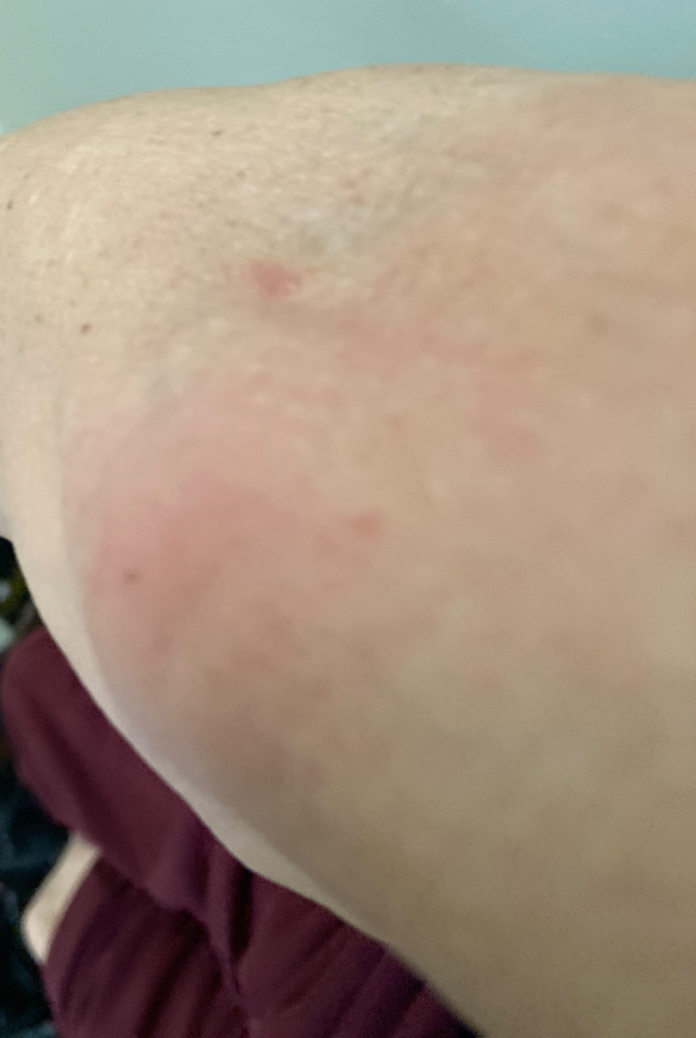Findings:
The skin findings could not be characterized from the image.
Background:
The patient considered this a rash. The subject is 60–69, male. The condition has been present for less than one week. The affected area is the front of the torso, arm, back of the hand and leg. An image taken at an angle. Associated systemic symptoms include shortness of breath. The lesion is described as raised or bumpy. Reported lesion symptoms include itching.